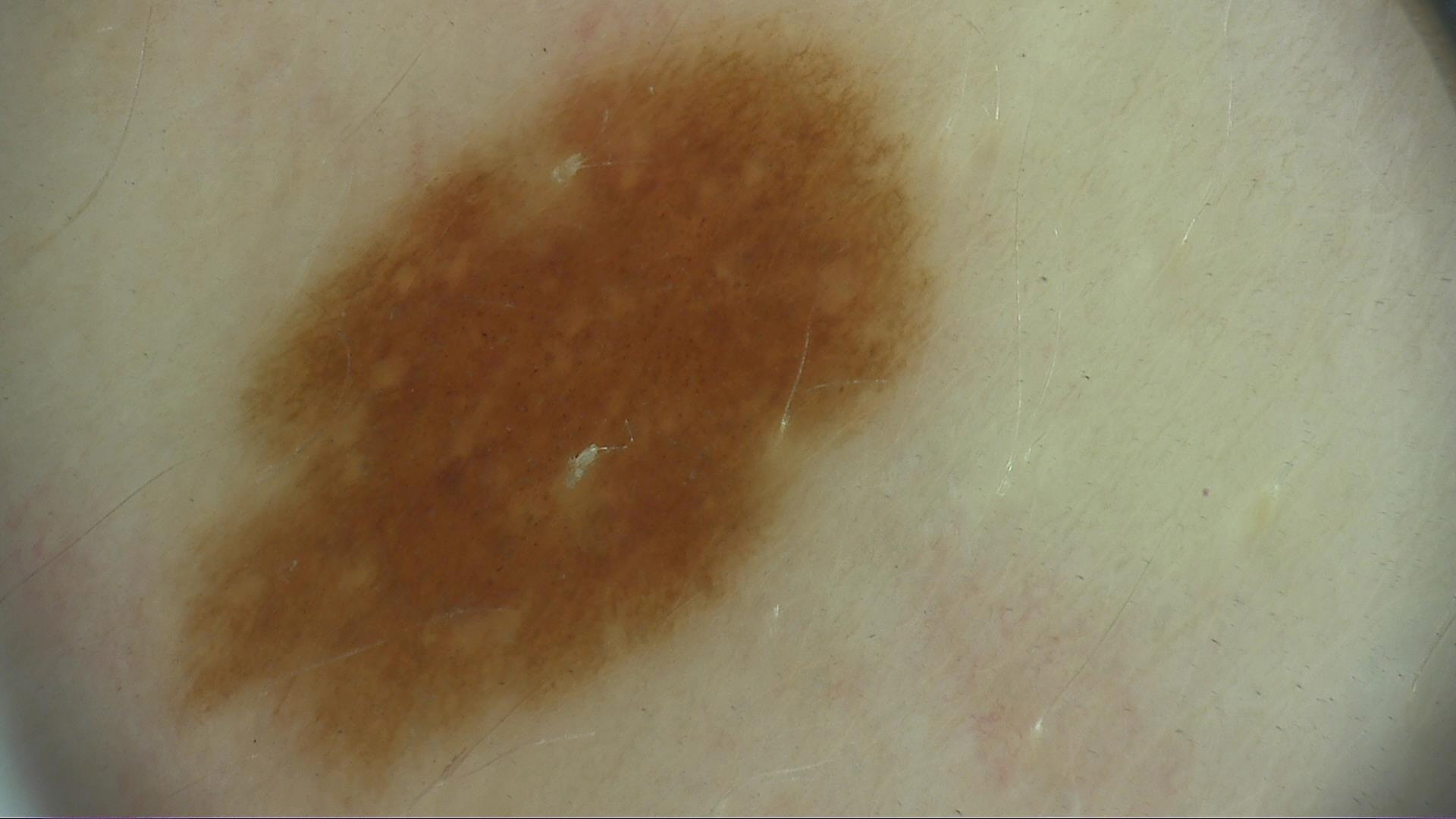Impression:
Classified as a dysplastic junctional nevus.